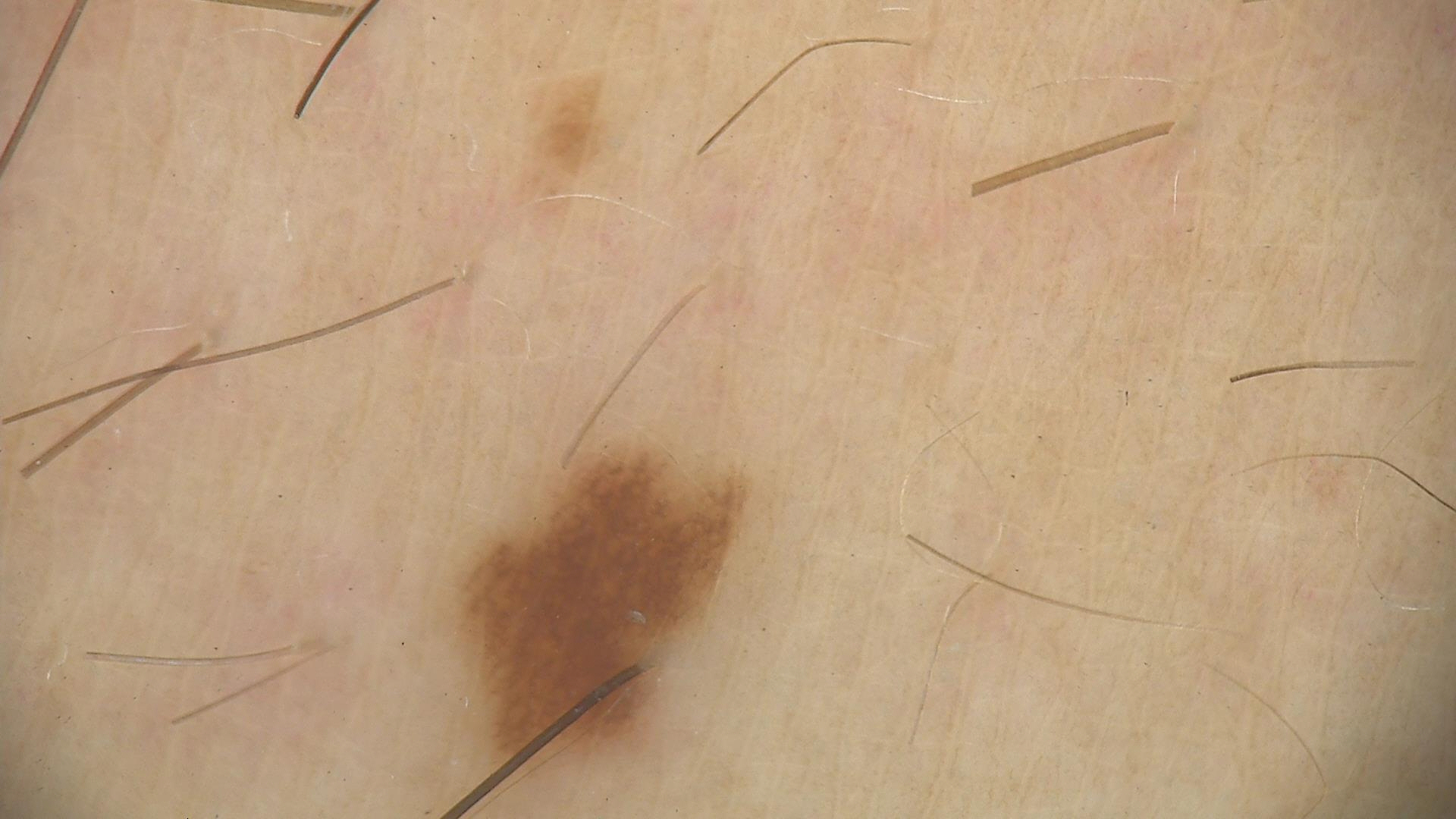modality: dermatoscopy | class: junctional nevus (expert consensus).